The patient says their skin reddens with sun exposure; collected as part of a research study, without a referral diagnosis; a dermatoscopic image of a skin lesion: 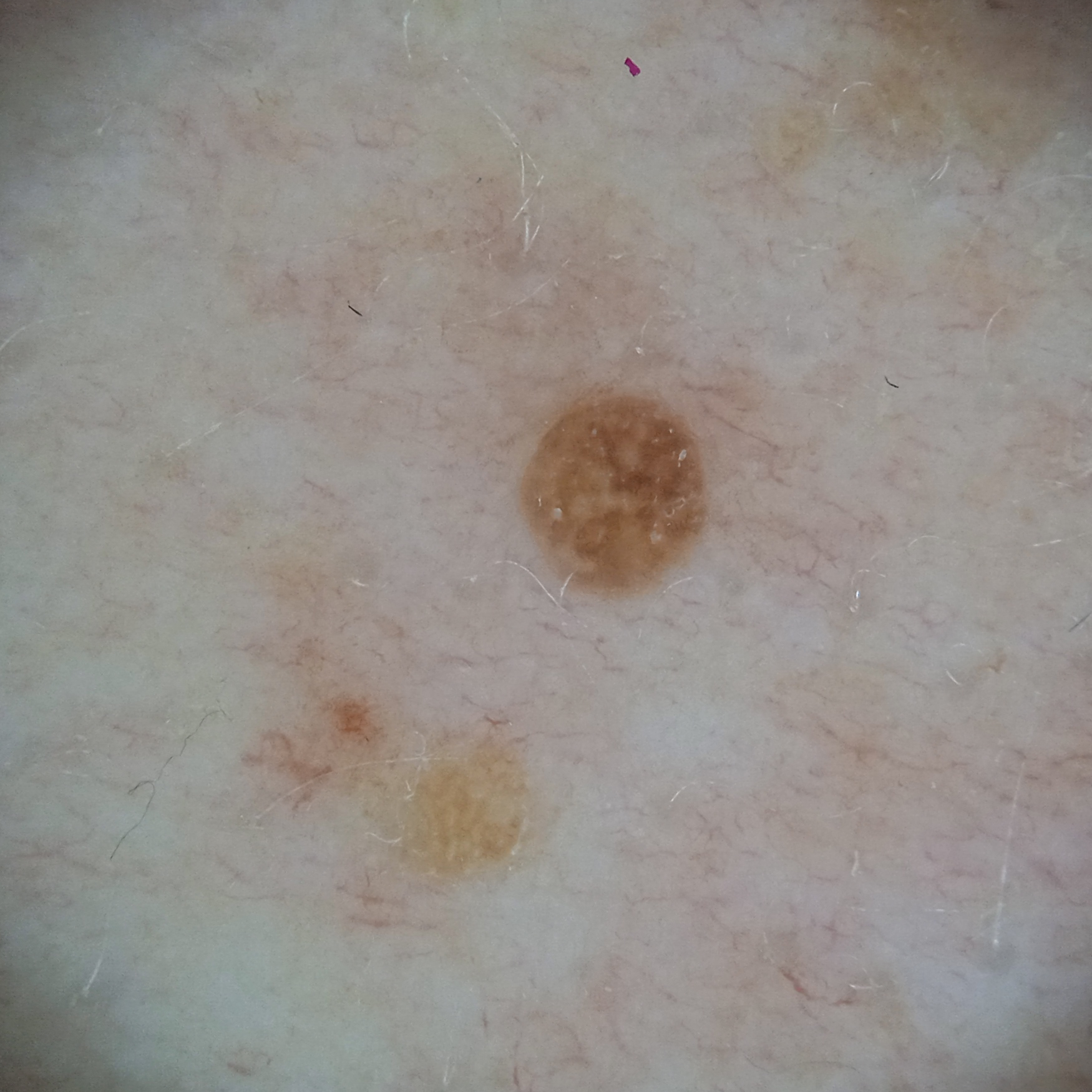<case>
  <lesion_size>
    <diameter_mm>2.2</diameter_mm>
  </lesion_size>
  <diagnosis>
    <name>seborrheic keratosis</name>
    <malignancy>benign</malignancy>
  </diagnosis>
</case>